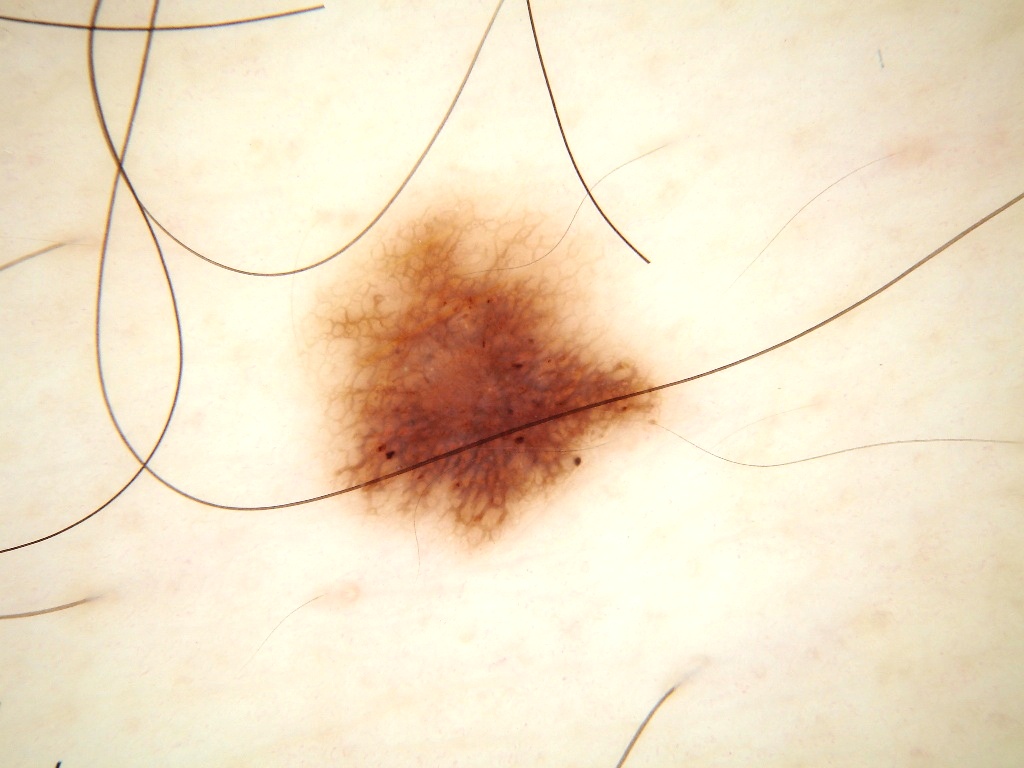Image and clinical context: A dermoscopic close-up of a skin lesion. As (left, top, right, bottom), the lesion's extent is box(278, 172, 713, 577). Dermoscopically, the lesion shows pigment network and globules; no negative network, milia-like cysts, or streaks. Conclusion: Clinically diagnosed as a melanocytic nevus, a benign lesion.